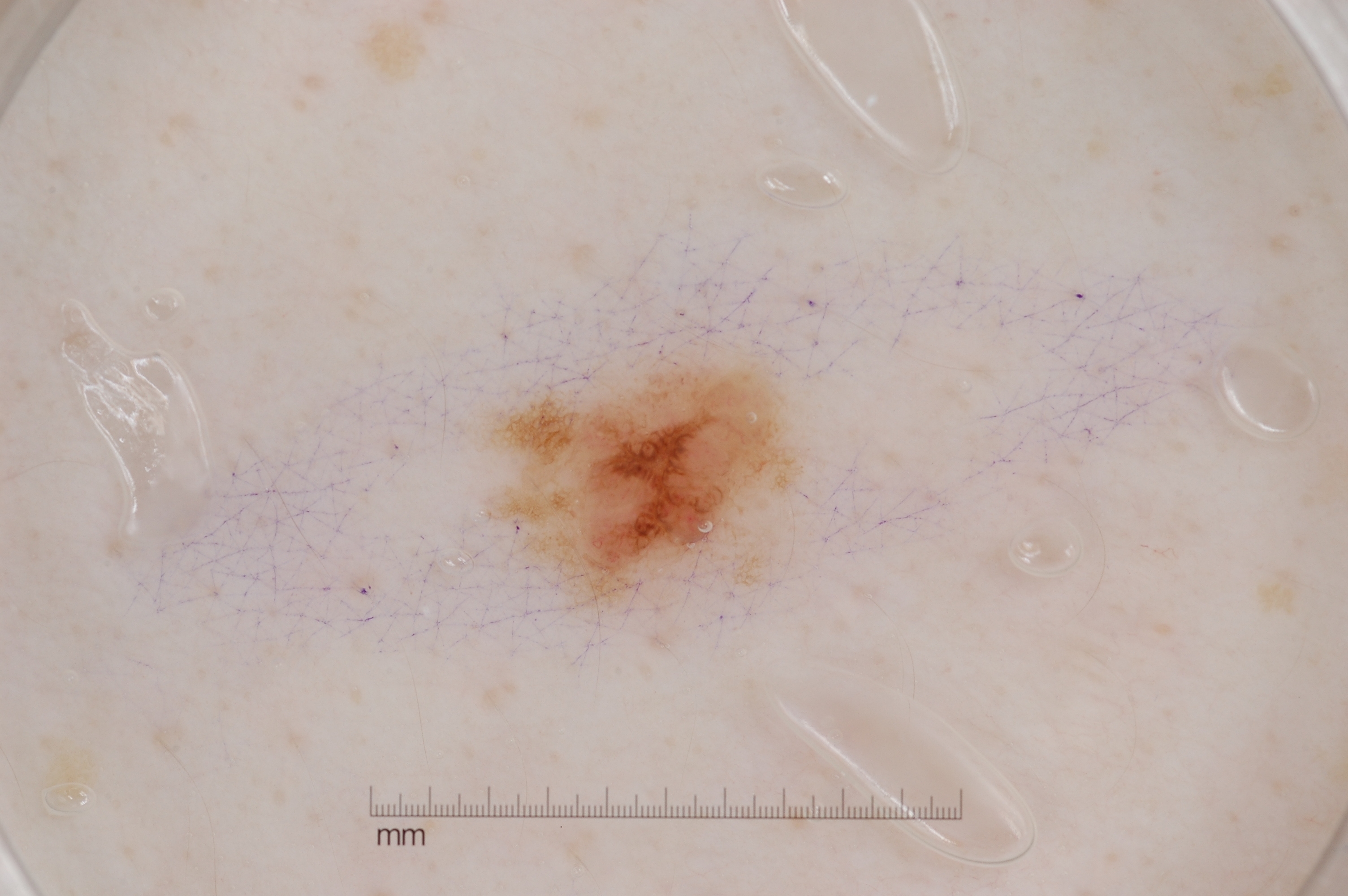Case summary:
- modality — dermoscopic image
- subject — female, in their 30s
- features — pigment network; absent: streaks, milia-like cysts, and negative network
- lesion bbox — x1=465 y1=333 x2=828 y2=631
- impression — a melanocytic nevus